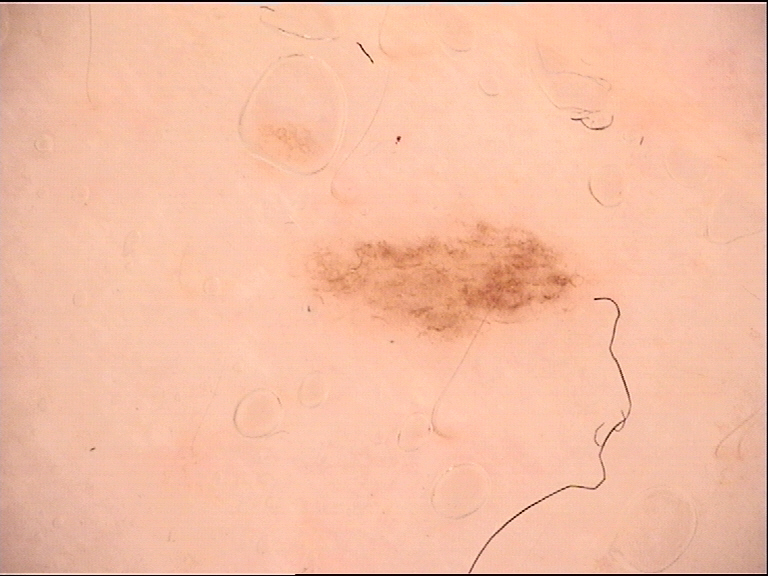<lesion>
<diagnosis>
<name>dysplastic junctional nevus</name>
<code>jd</code>
<malignancy>benign</malignancy>
<super_class>melanocytic</super_class>
<confirmation>expert consensus</confirmation>
</diagnosis>
</lesion>